Located on the leg. This is a close-up image:
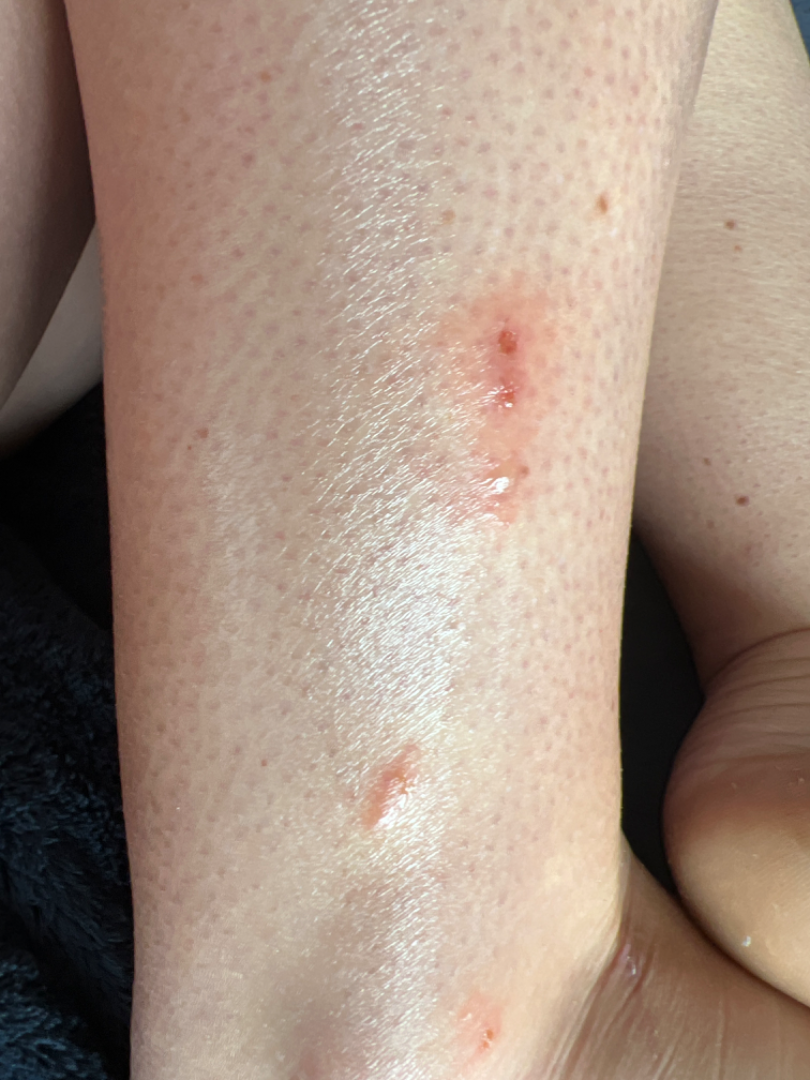On photographic review, in keeping with Folliculitis.